A dermatoscopic image of a skin lesion.
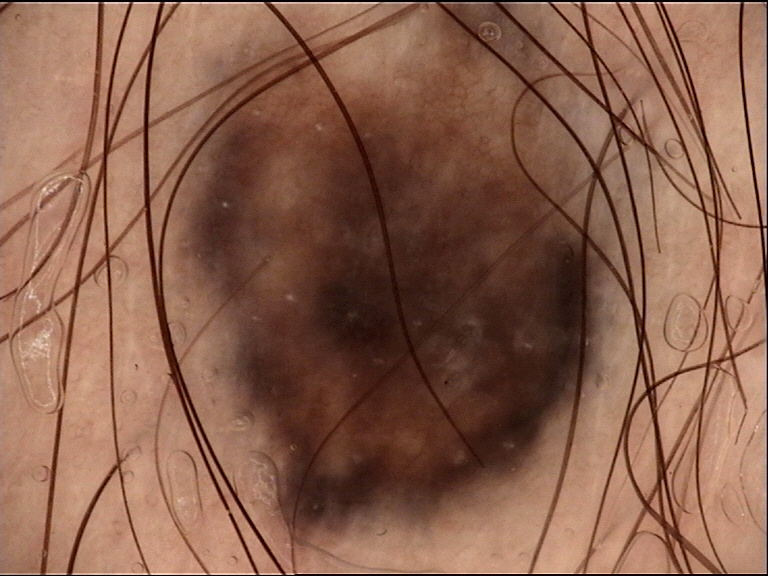  diagnosis:
    name: blue nevus
    code: bdb
    malignancy: benign
    super_class: melanocytic
    confirmation: expert consensus